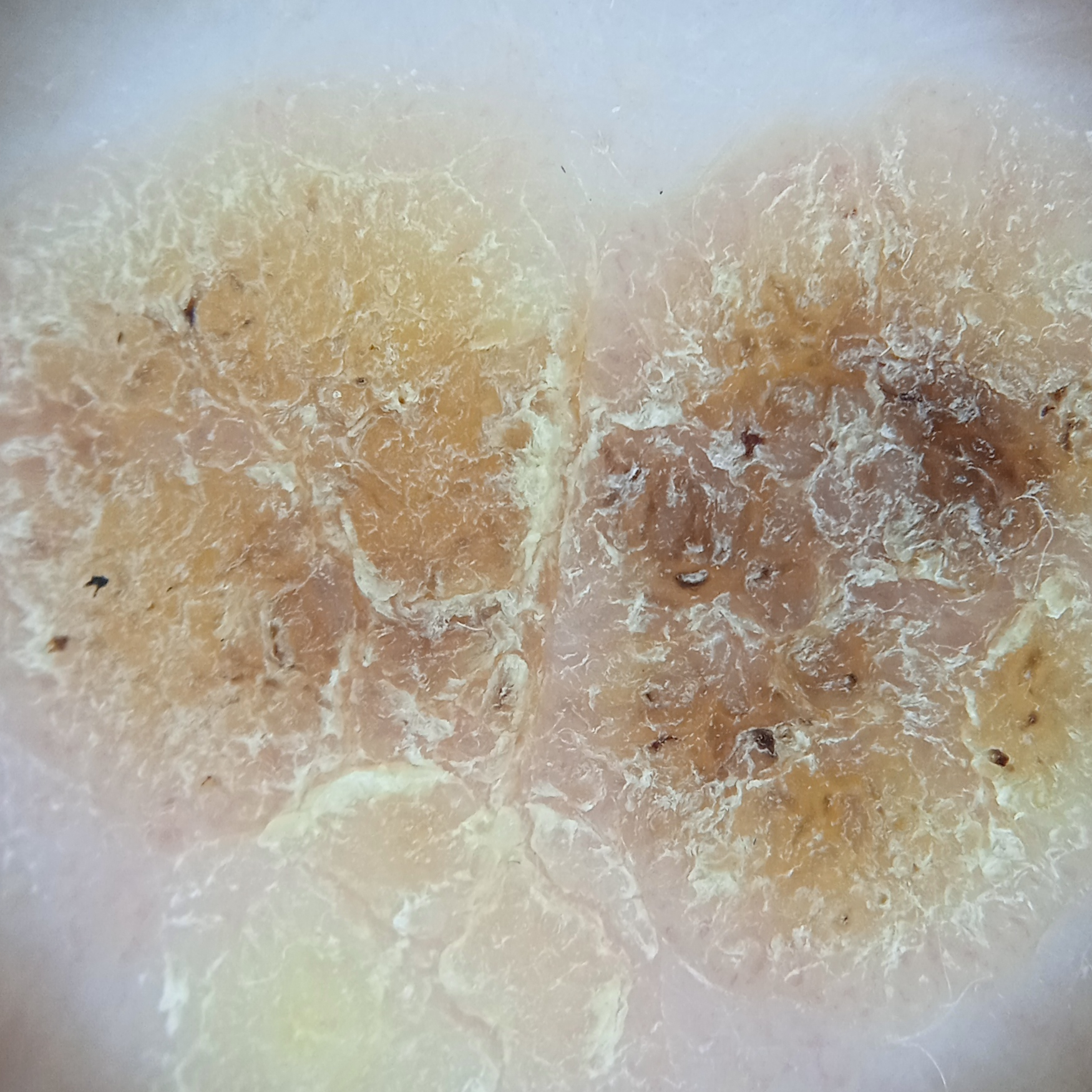Q: What was the diagnosis?
A: seborrheic keratosis (dermatologist consensus)